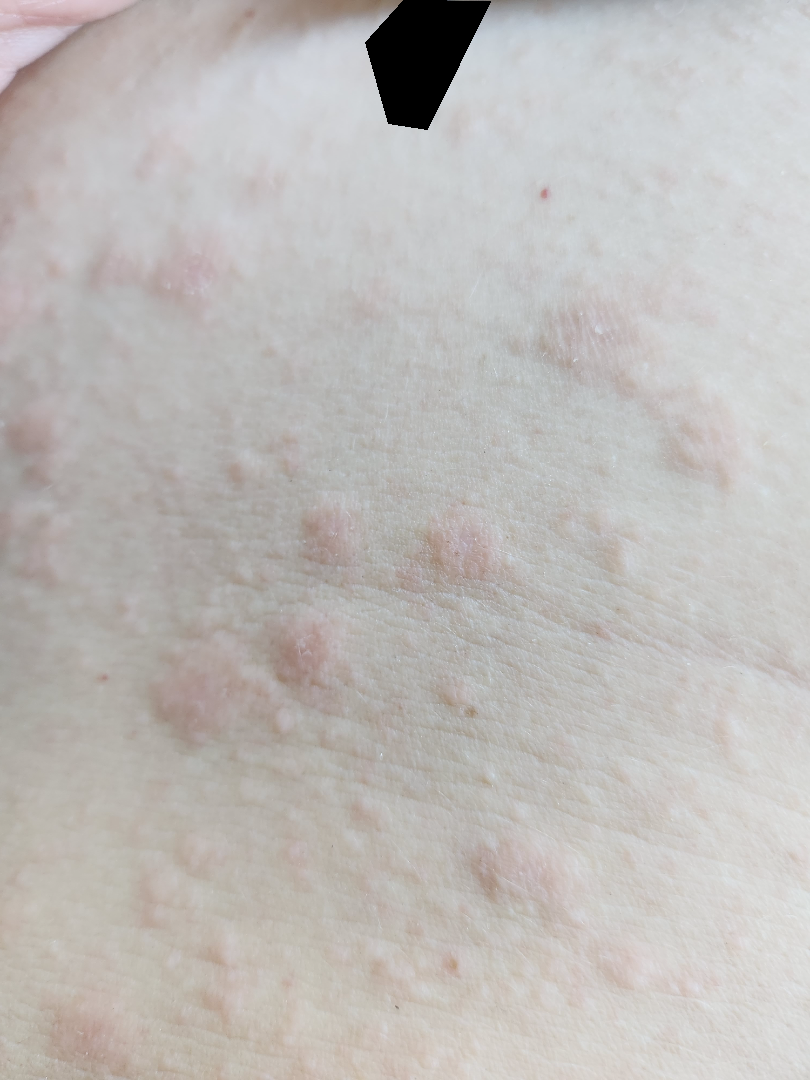{
  "assessment": "indeterminate",
  "body_site": [
    "head or neck",
    "back of the torso",
    "arm",
    "front of the torso"
  ],
  "shot_type": "close-up"
}